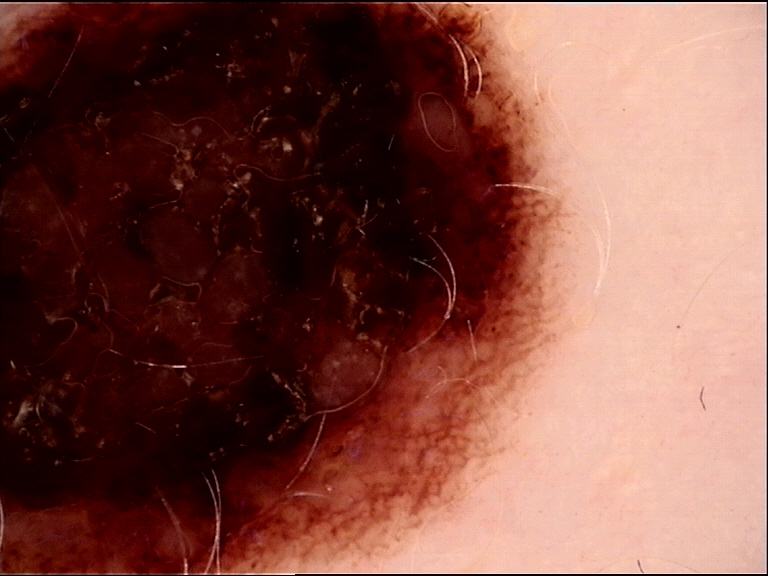Q: What was the diagnostic impression?
A: dysplastic compound nevus (expert consensus)